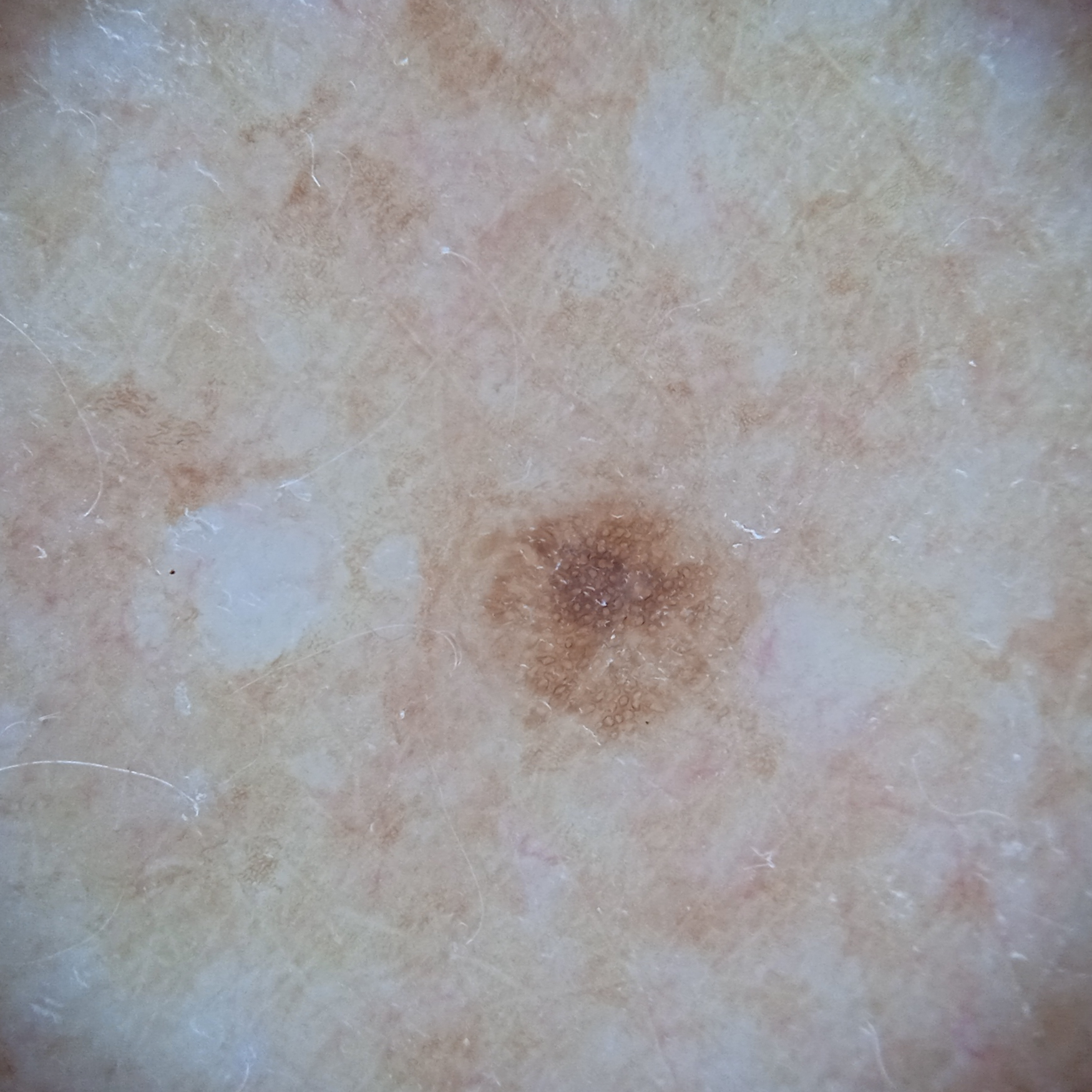Dermatologist review favored a melanocytic nevus.